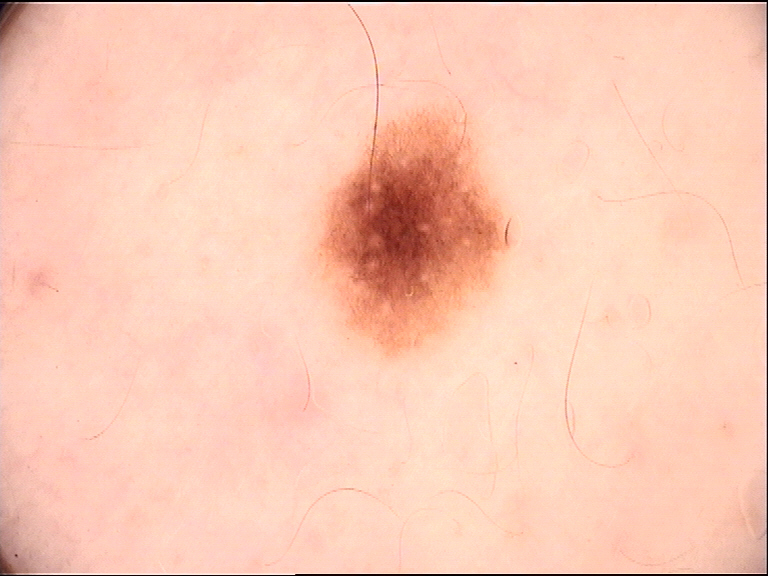imaging: dermatoscopy; diagnostic label: dysplastic junctional nevus (expert consensus).